A patient 53 years of age. A clinical photograph of a skin lesion.
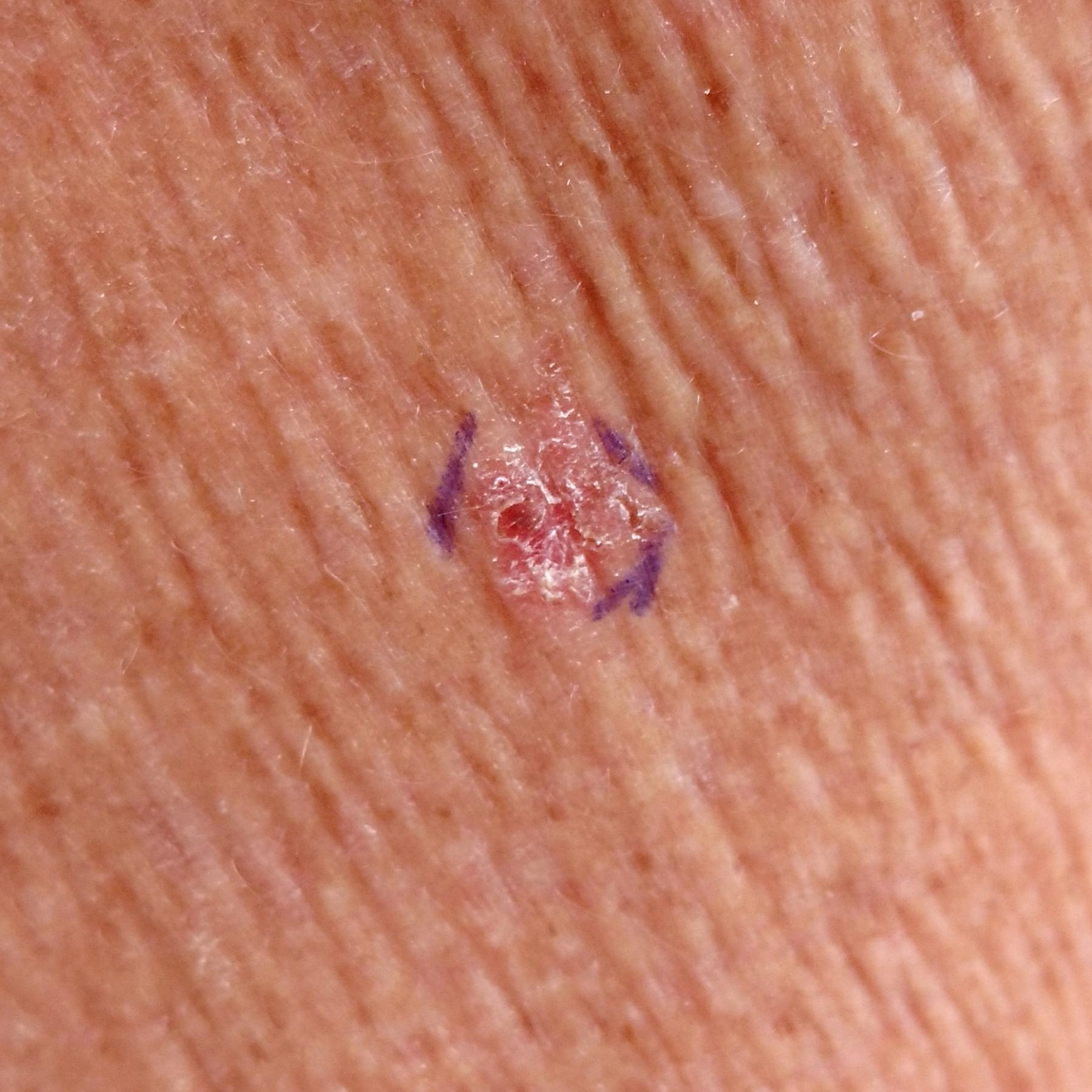anatomic site — an arm
assessment — actinic keratosis (clinical consensus)